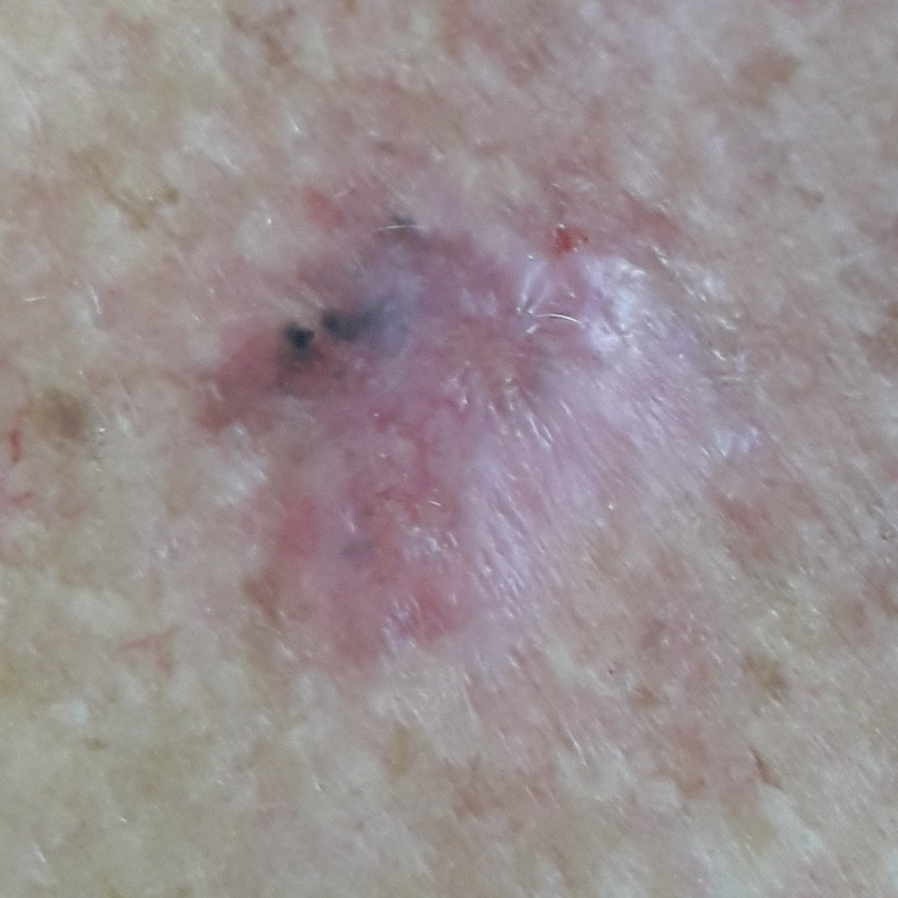risk_factors:
  positive:
    - prior skin cancer (patient or family)
image: clinical photograph
patient:
  age: 57
  gender: male
diagnosis:
  name: basal cell carcinoma
  code: BCC
  malignancy: malignant
  confirmation: histopathology